Close-up view. The back of the torso and leg are involved:
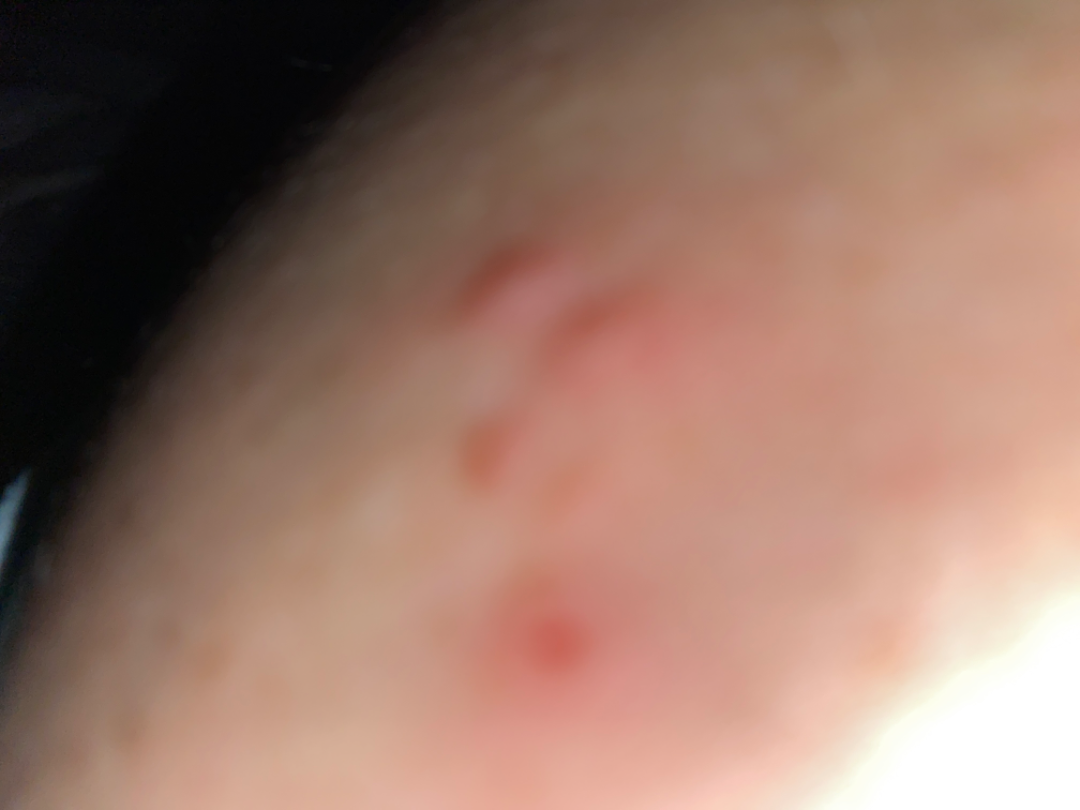Assessment: Diagnostic features were not clearly distinguishable in this photograph. Clinical context: The patient reported no systemic symptoms. The lesion is associated with bothersome appearance and pain. Self-categorized by the patient as skin that appeared healthy to them. The contributor reports the condition has been present for one to four weeks. Texture is reported as raised or bumpy.